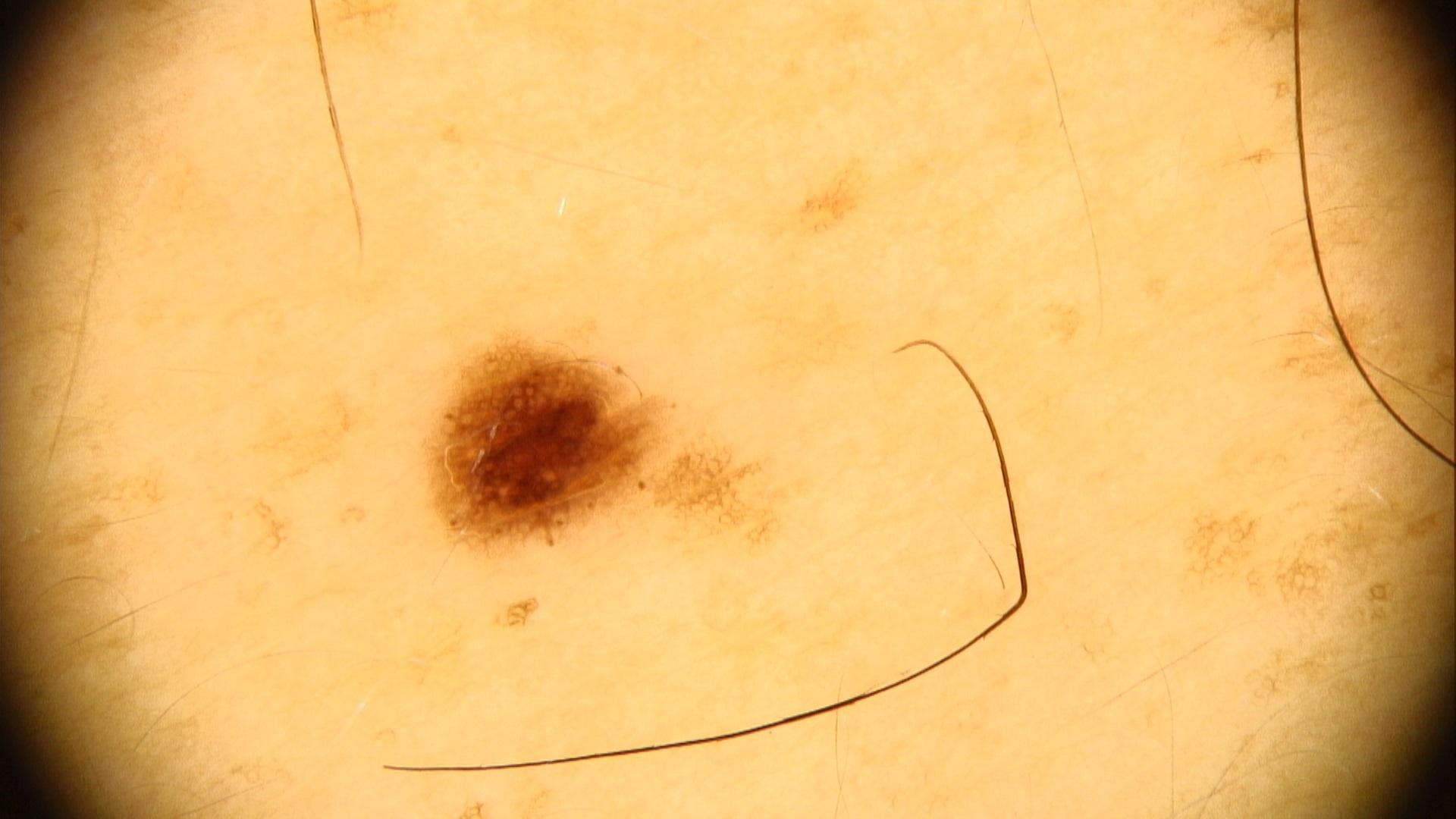Summary: The patient is Fitzpatrick III. A dermoscopic photograph of a skin lesion. A male subject aged around 40. Conclusion: The clinical impression was a lesion of melanocytic lineage — a nevus.